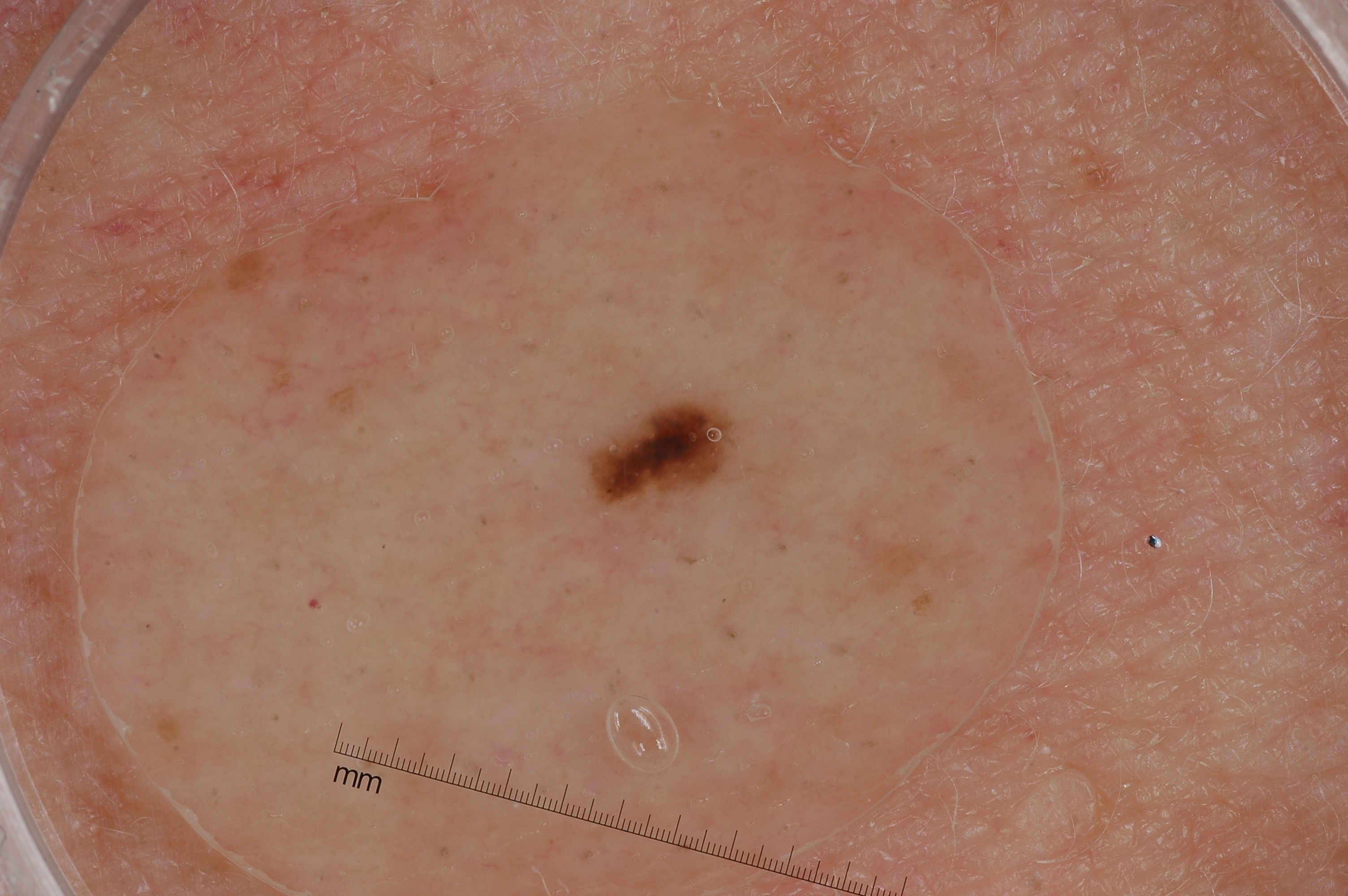A dermoscopic view of a skin lesion. The subject is a male aged approximately 45. Dermoscopic review identifies no streaks, pigment network, negative network, or milia-like cysts. The lesion is bounded by 590/399/726/497. The diagnostic assessment was a melanocytic nevus, a benign skin lesion.